The lesion involves the head or neck; the photo was captured at an angle: 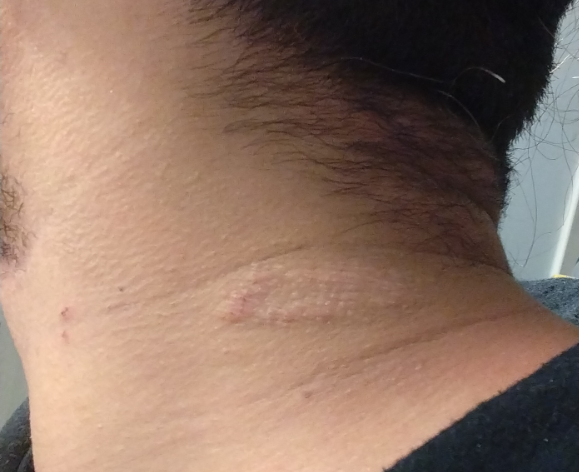Review: The reviewing dermatologist was unable to assign a differential diagnosis from the image. Patient information: Present for one to four weeks. Skin tone: Fitzpatrick phototype IV; non-clinician graders estimated Monk skin tone scale 3 or 4. Reported lesion symptoms include itching and enlargement. Self-categorized by the patient as a rash.